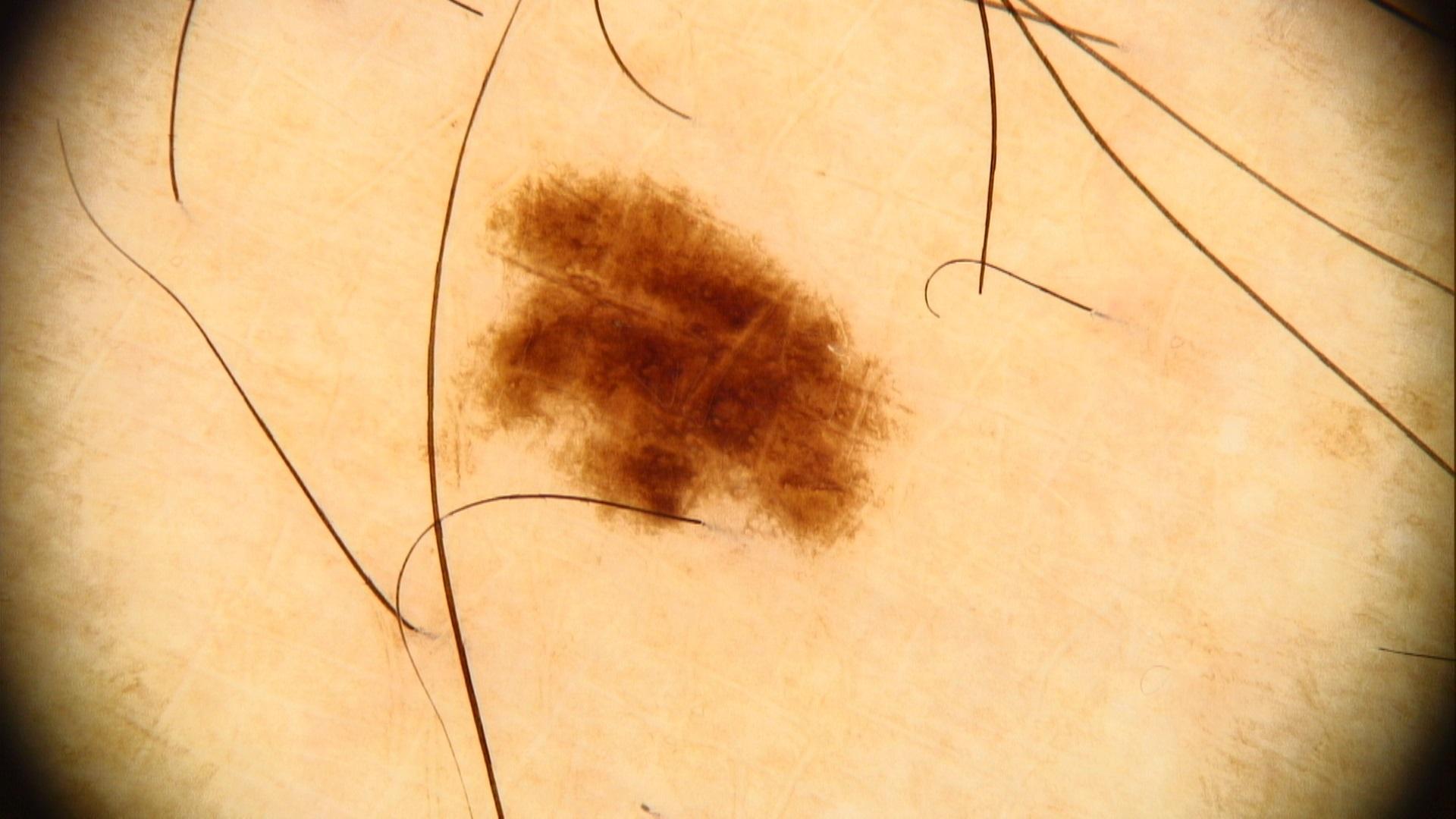The chart documents no previous melanoma and no first-degree relative with melanoma.
A male patient aged 58 to 62.
The patient is Fitzpatrick phototype III.
Dermoscopy of a skin lesion.
The lesion is on a lower extremity.
The clinical impression was a benign lesion — a nevus.